Close-up view. The affected area is the arm. Male patient, age 50–59 — 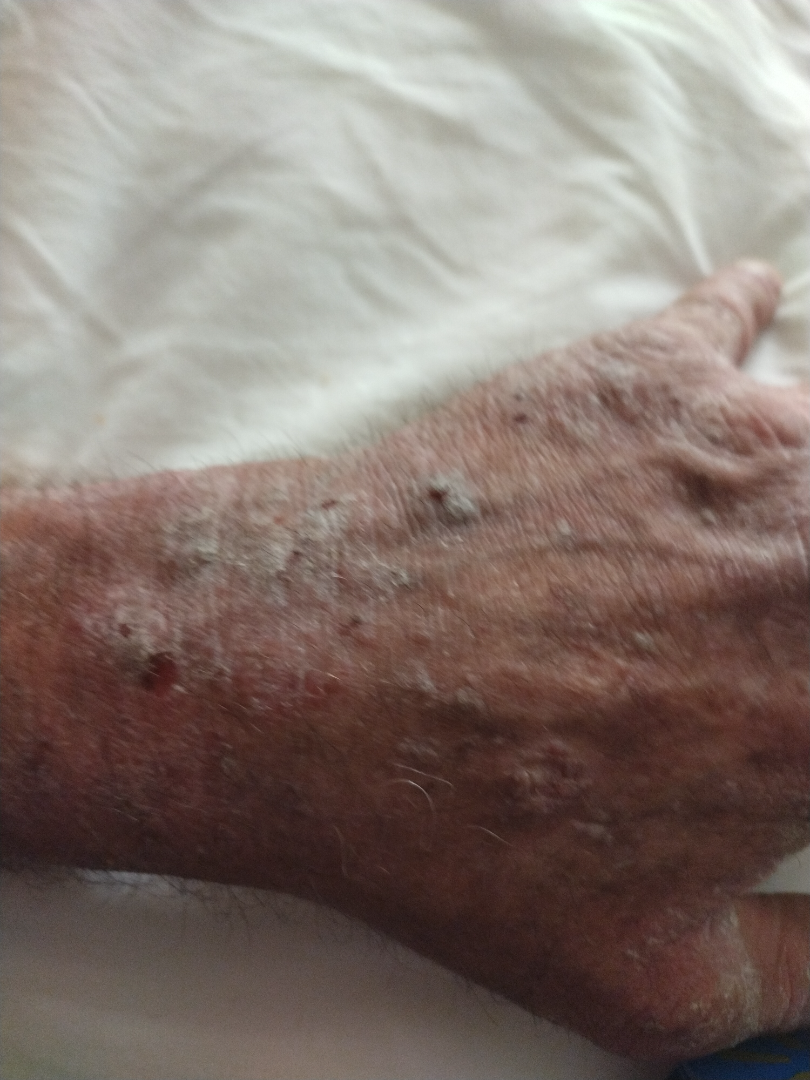The patient considered this a rash. The contributor reports itching, darkening, enlargement and bothersome appearance. Reported duration is more than one year. The contributor reports the lesion is raised or bumpy and rough or flaky. On dermatologist assessment of the image, the differential, in no particular order, includes Prurigo nodularis and Actinic Keratosis.